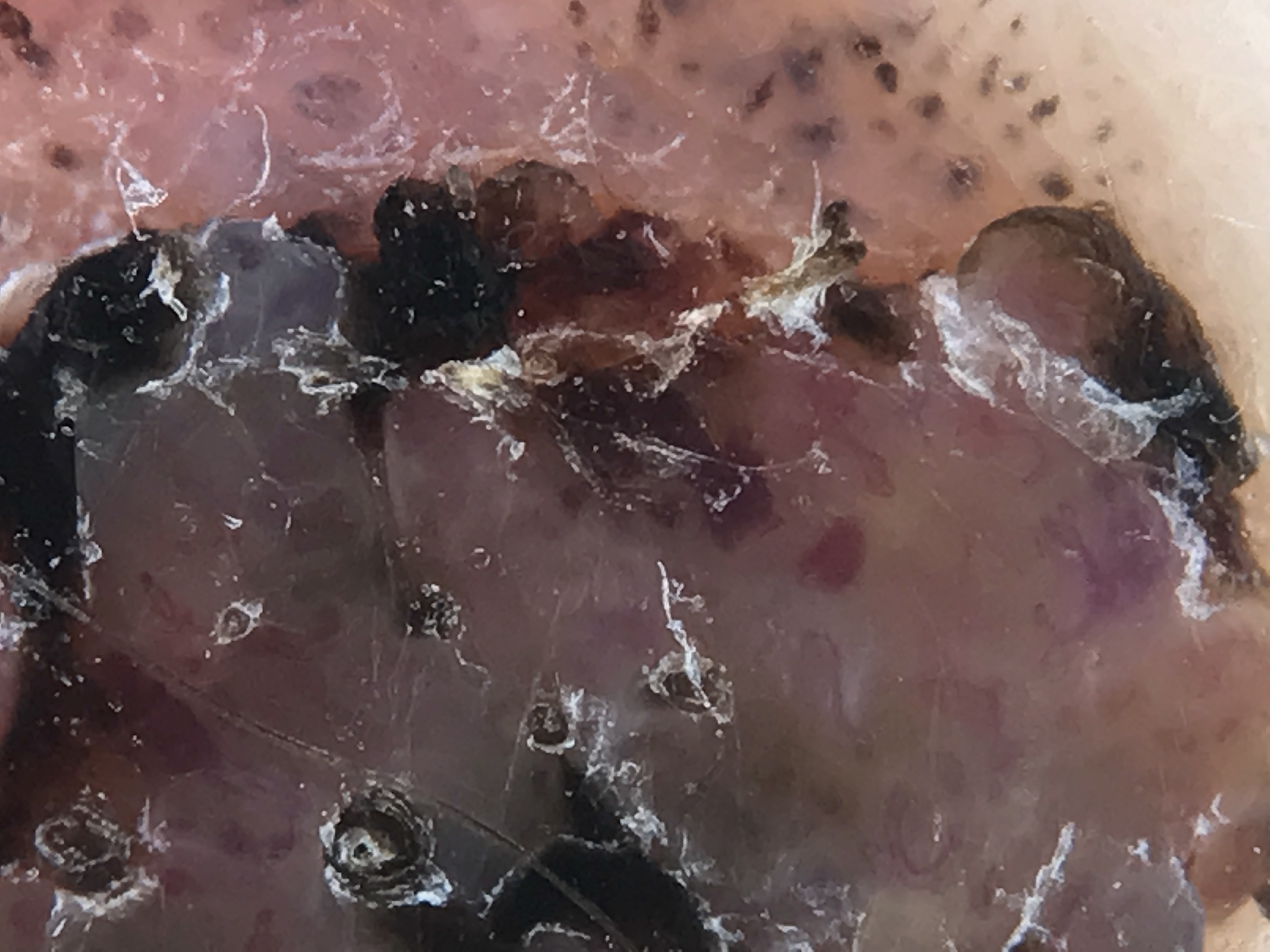The diagnostic label was a benign lesion — a congenital dysplastic compound nevus.